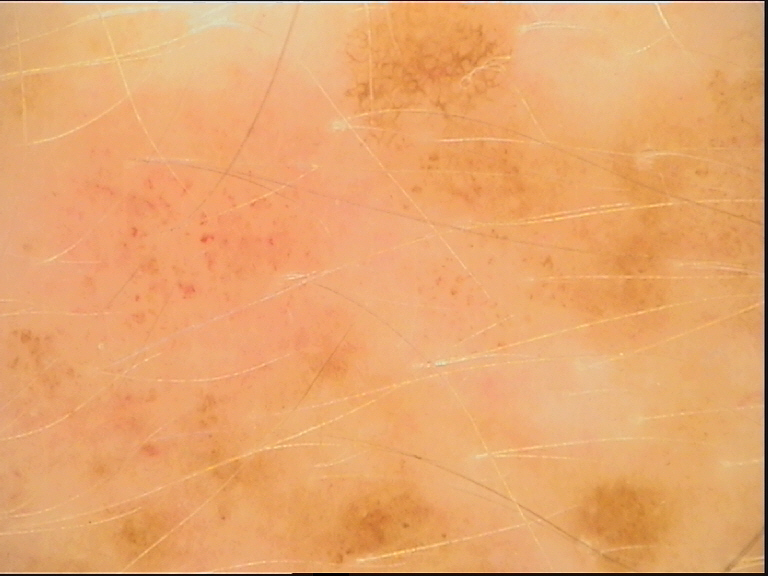Conclusion: The diagnosis was a dysplastic junctional nevus.